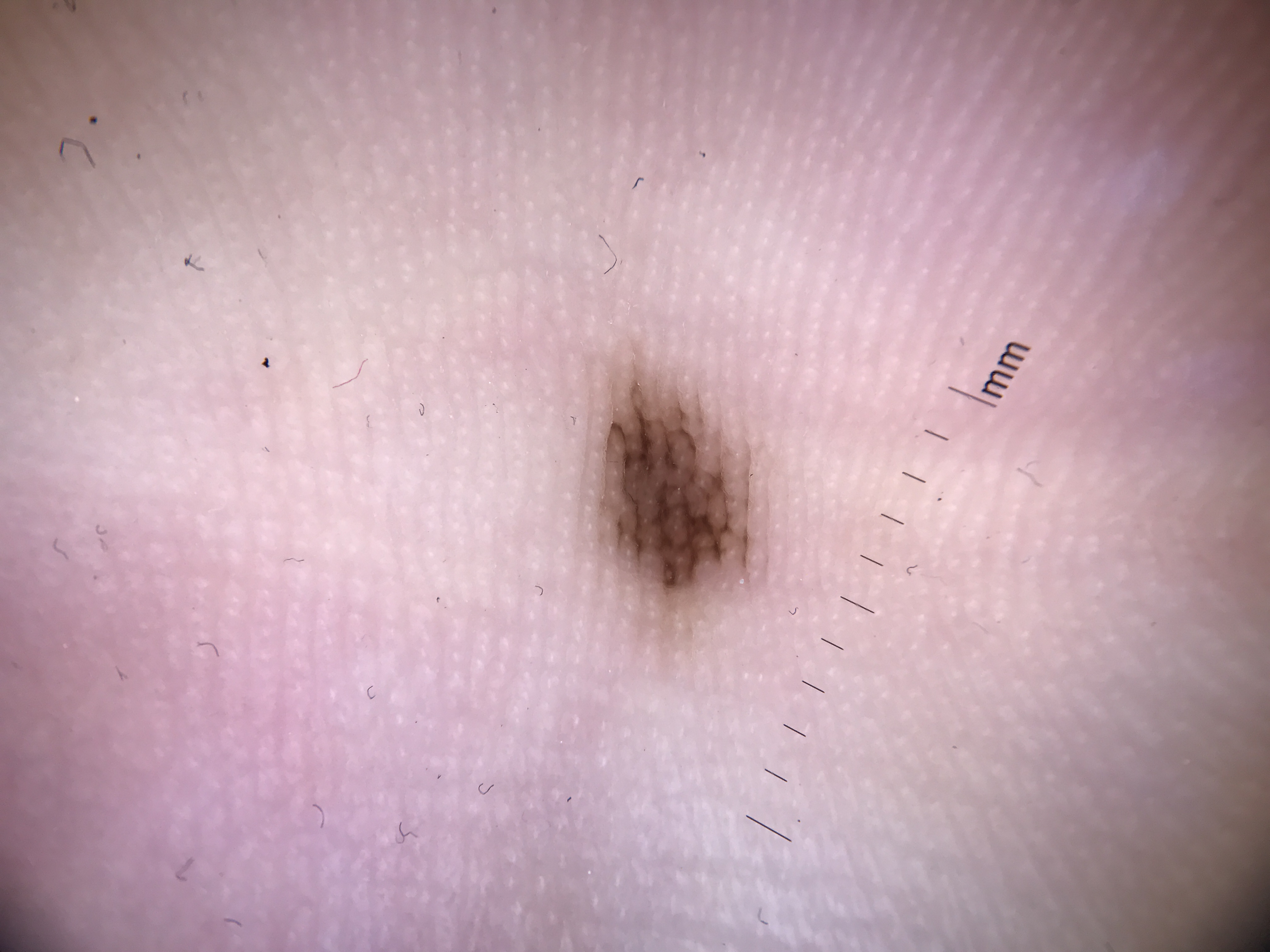• subtype — banal
• class — acral junctional nevus (expert consensus)